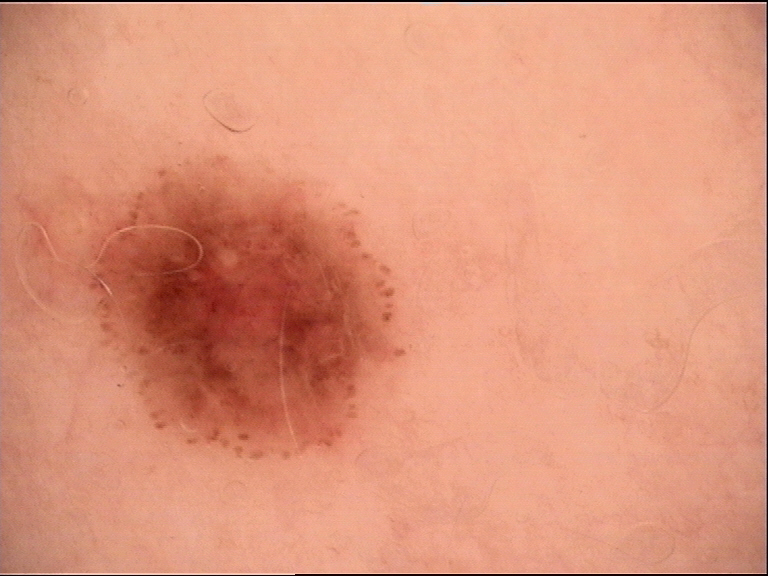Case:
- image — dermoscopy
- label — dysplastic compound nevus (expert consensus)